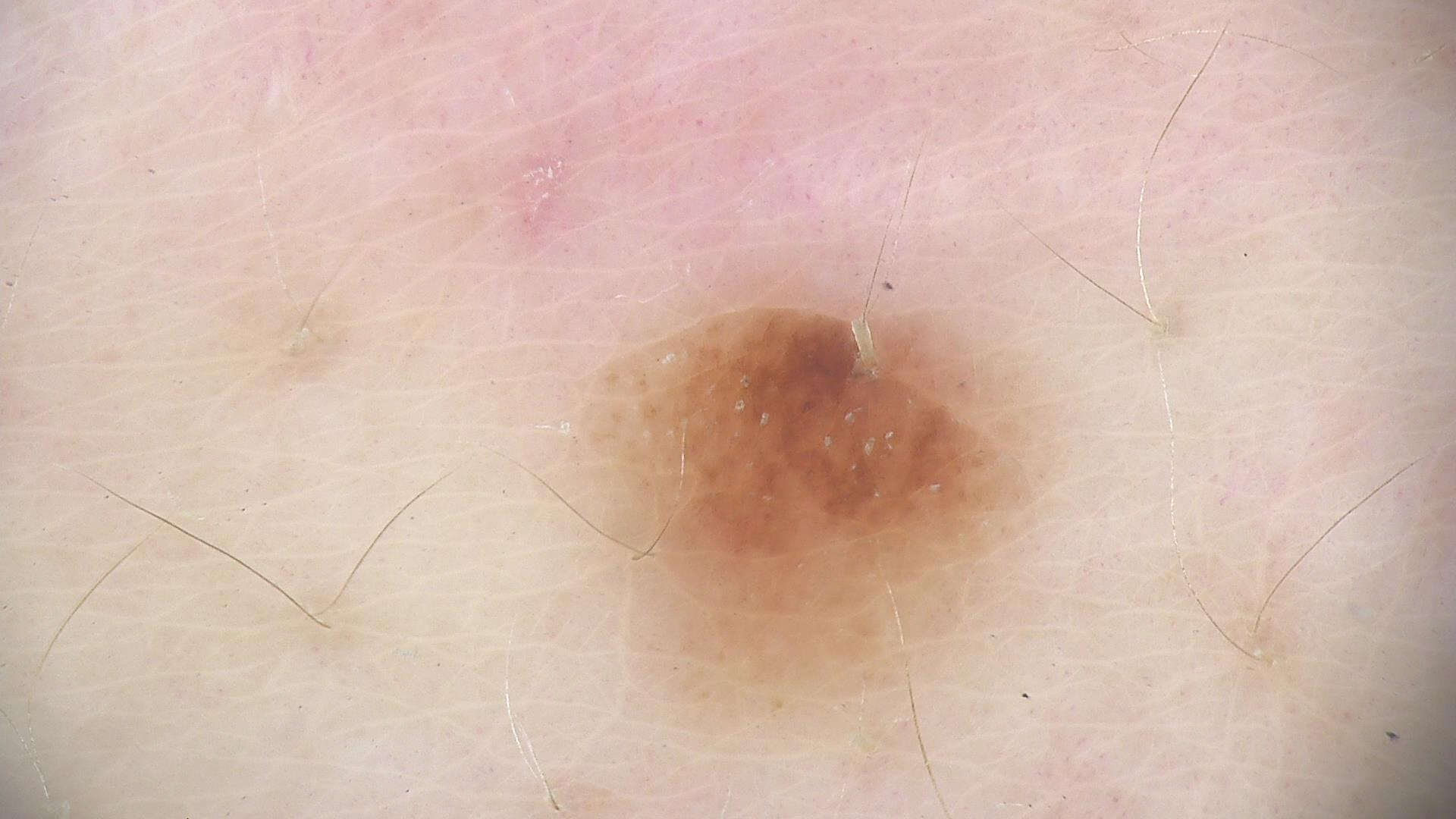Findings:
- imaging: dermatoscopy
- lesion type: banal
- label: compound nevus (expert consensus)